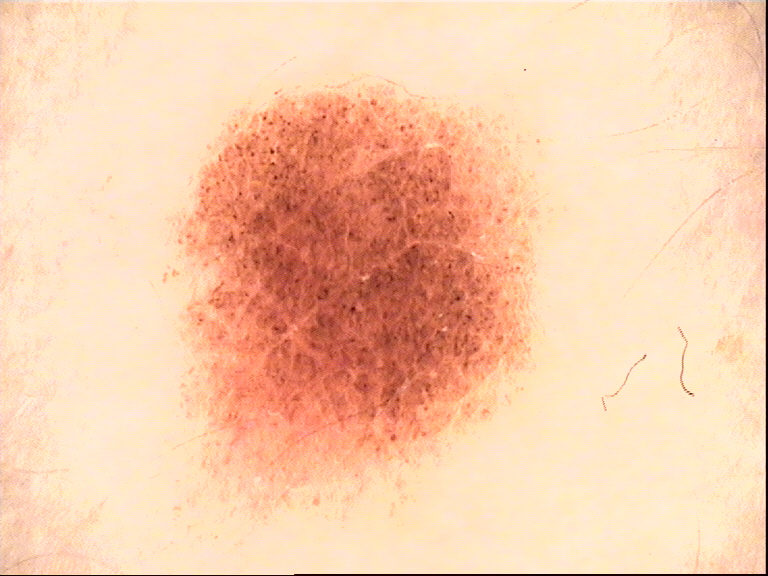label = dysplastic compound nevus (expert consensus).